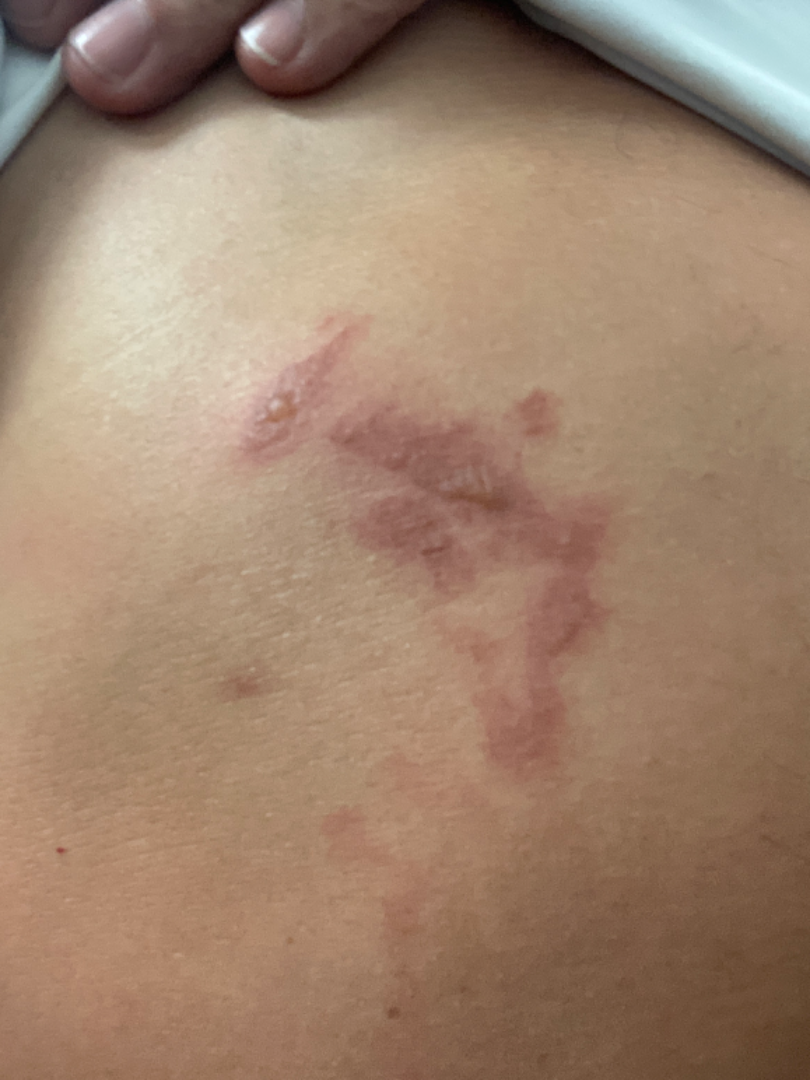The subject is male. The front of the torso is involved. The photograph is a close-up of the affected area. On photographic review by a dermatologist: Allergic Contact Dermatitis (0.67); Burn of skin (0.33).